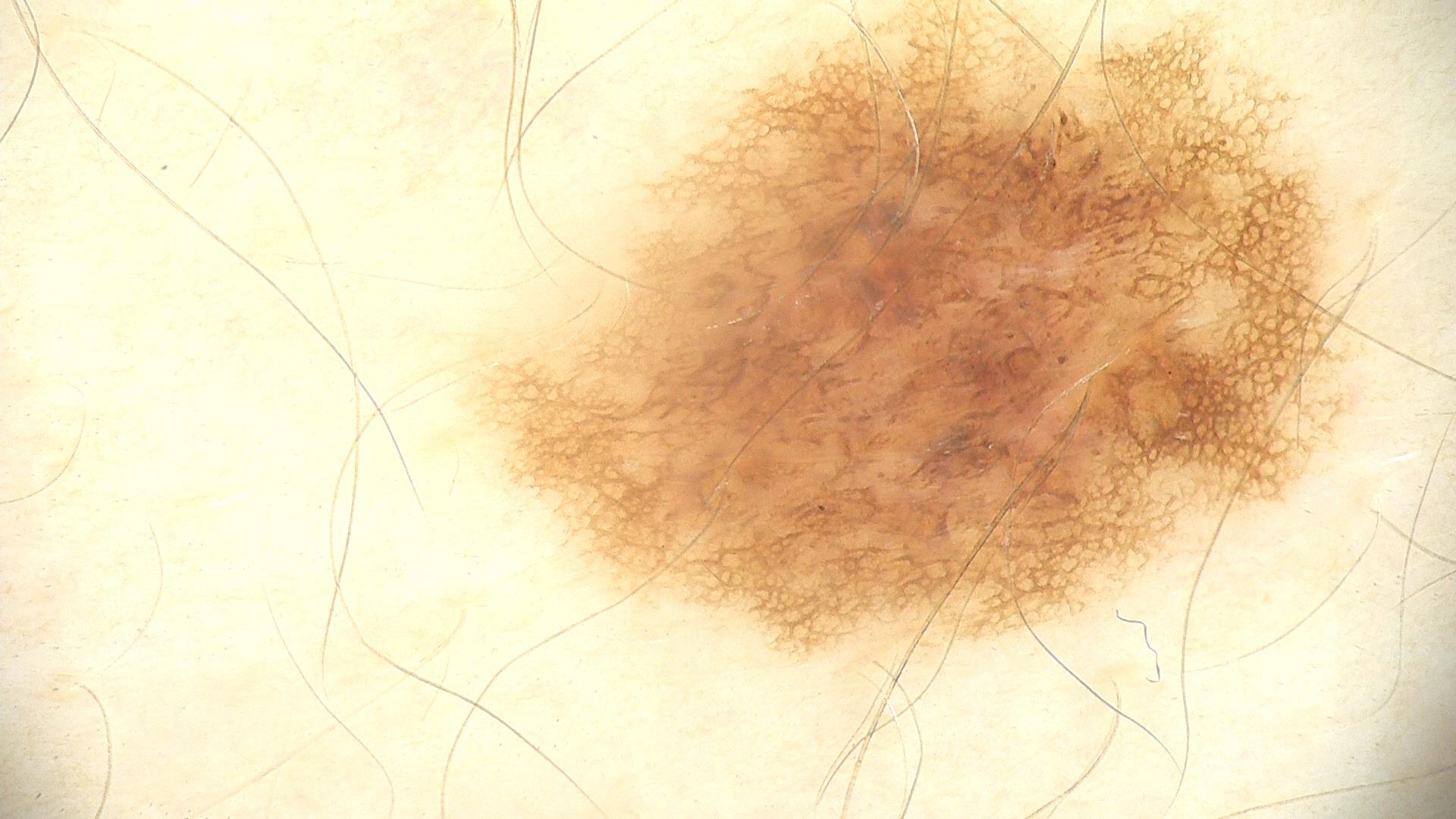Classified as a dysplastic junctional nevus.